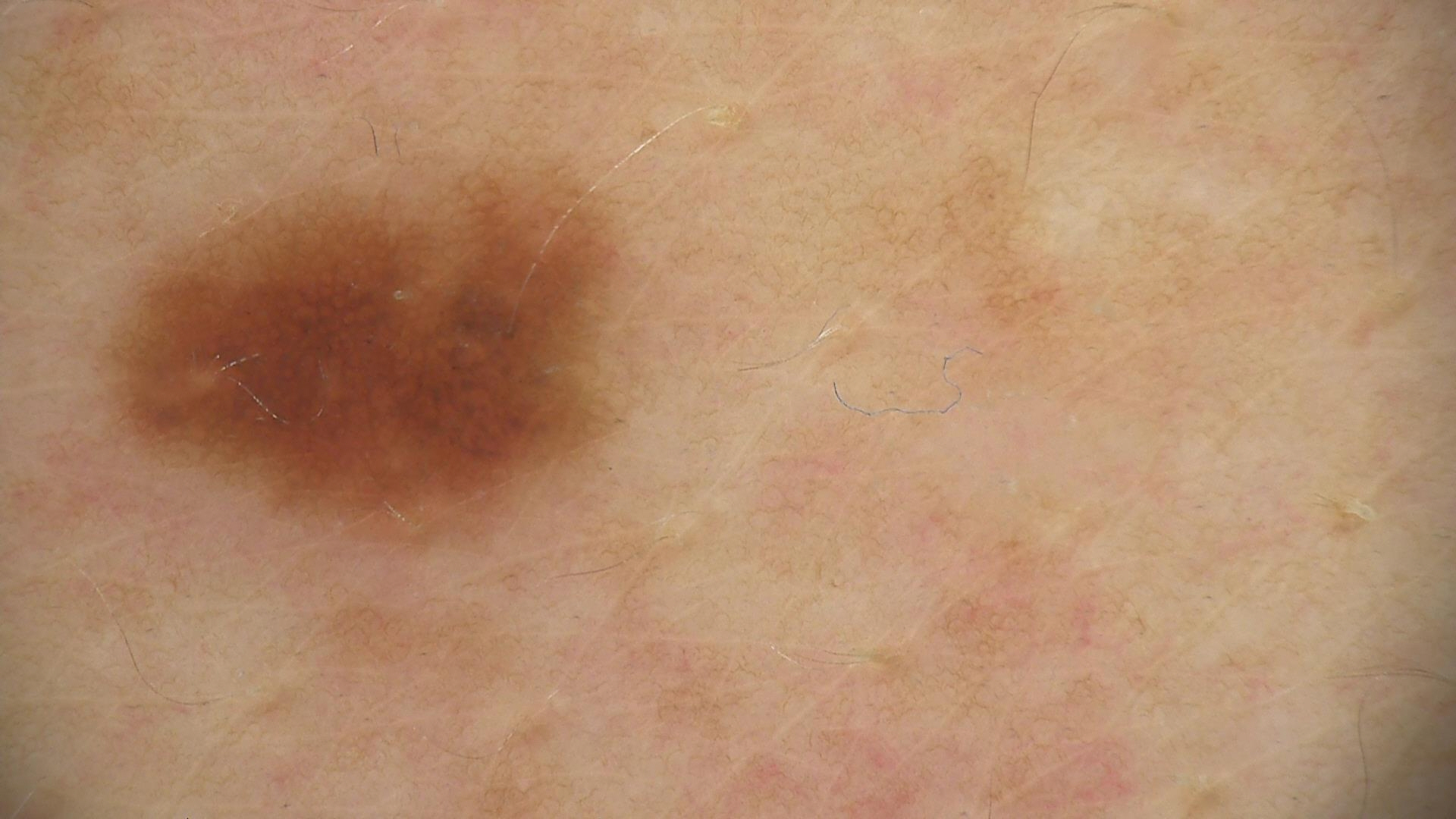{
  "image": "dermoscopy",
  "diagnosis": {
    "name": "dysplastic junctional nevus",
    "code": "jd",
    "malignancy": "benign",
    "super_class": "melanocytic",
    "confirmation": "expert consensus"
  }
}